This is a close-up image: 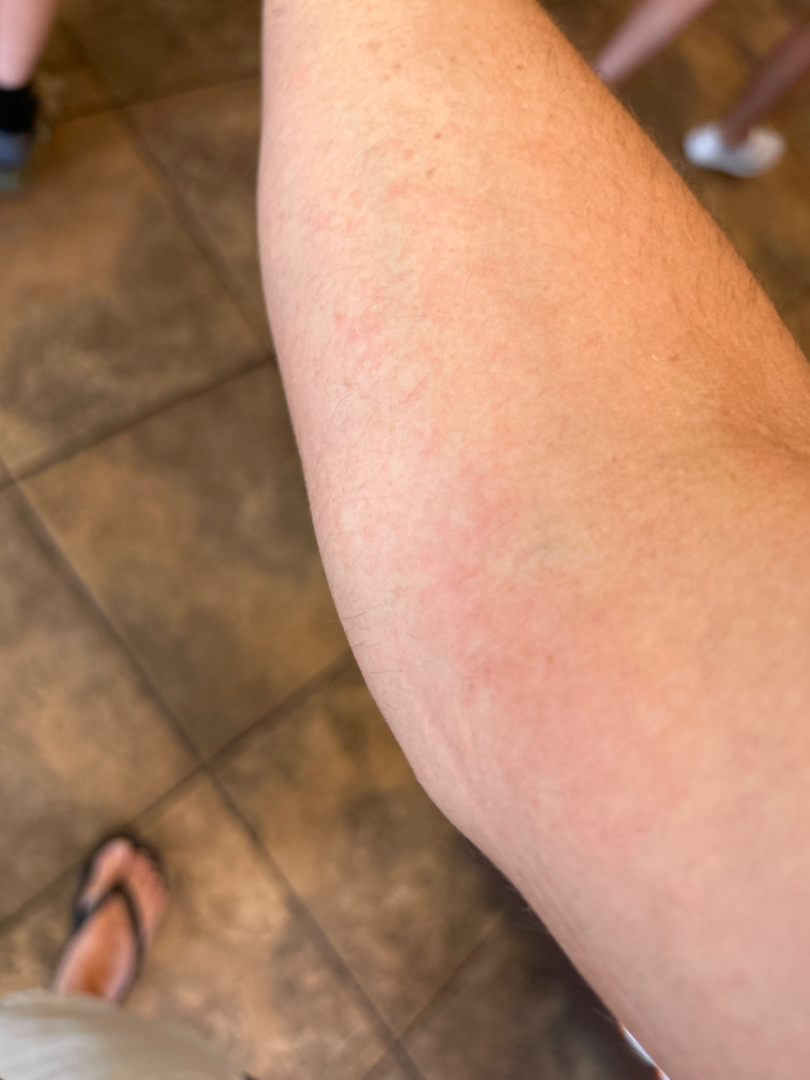impression=reviewed remotely by one dermatologist: consistent with Eczema